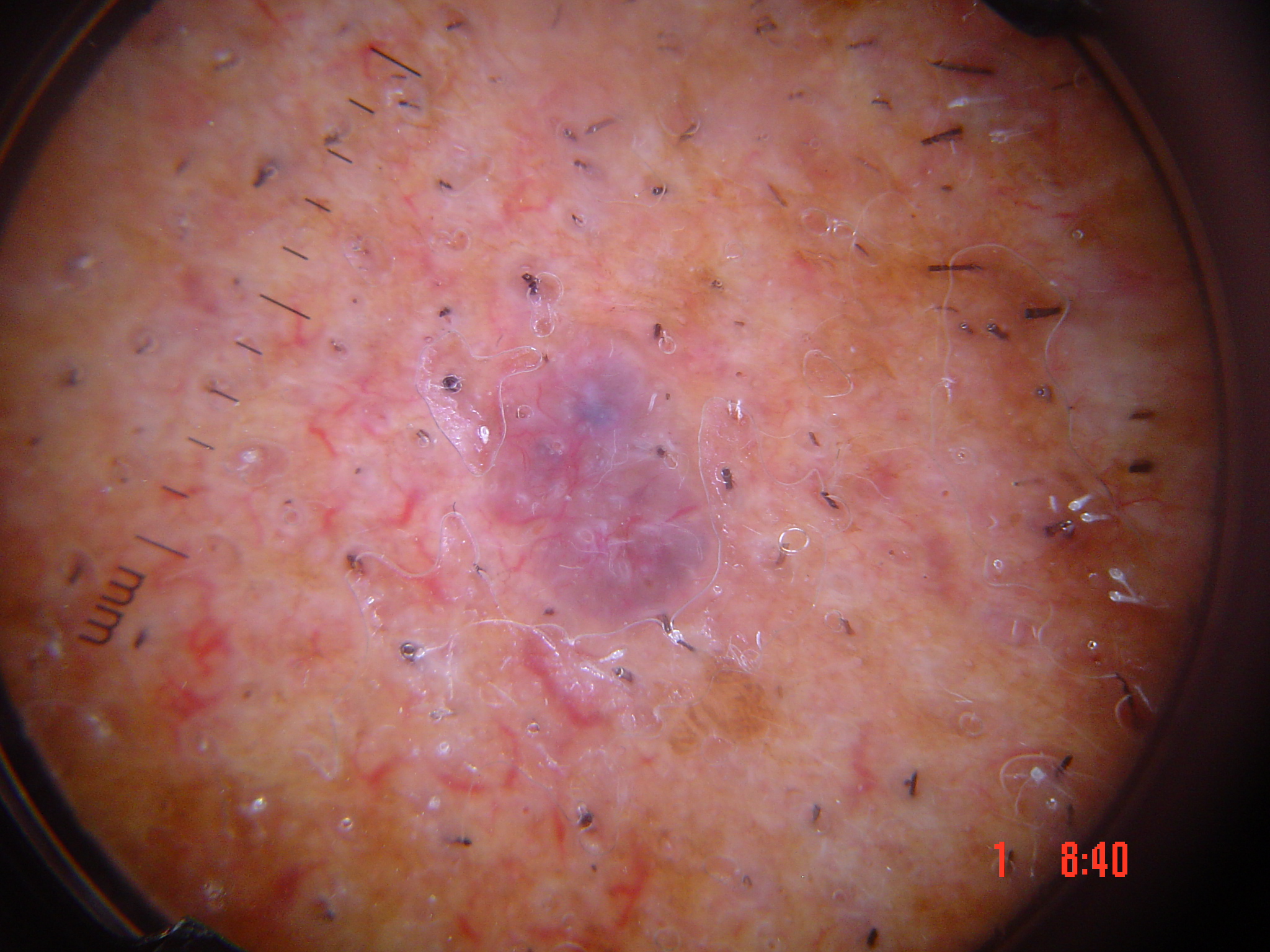Confirmed on histopathology as a basal cell carcinoma.